A patient 51 years of age:
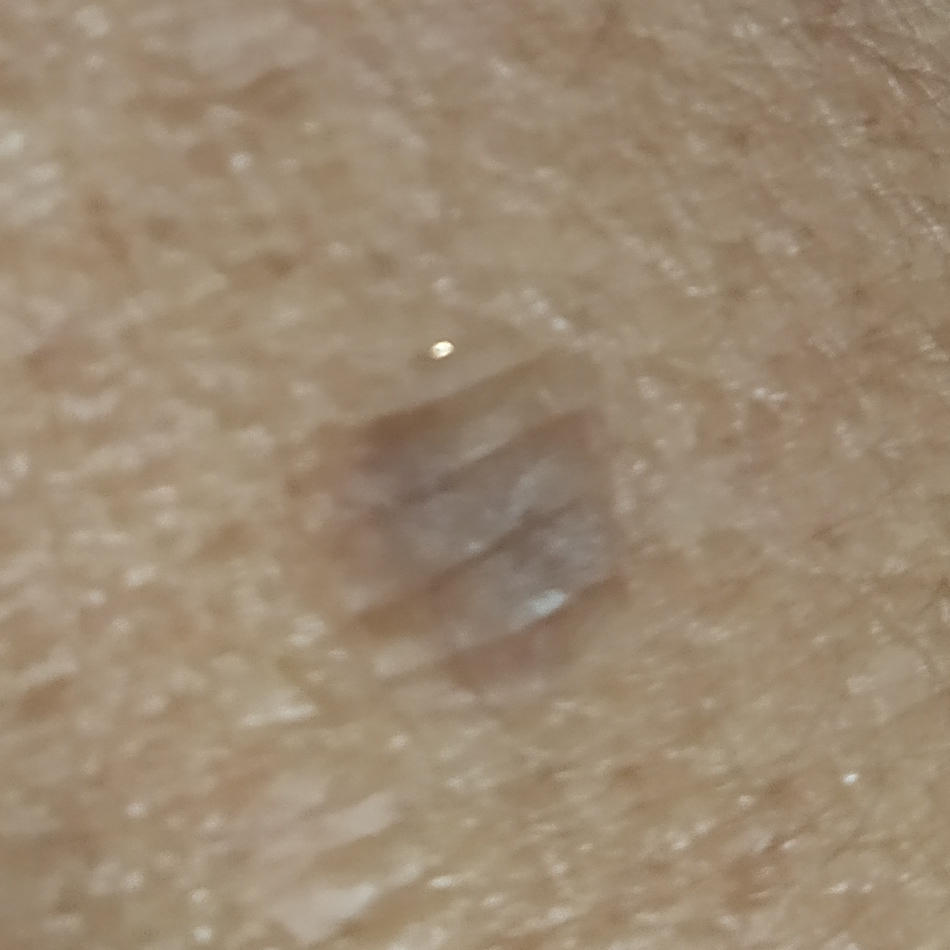Impression: Expert review favored a benign lesion — a seborrheic keratosis.